The patient is 18–29, male; the lesion involves the head or neck and arm; the photograph is a close-up of the affected area:
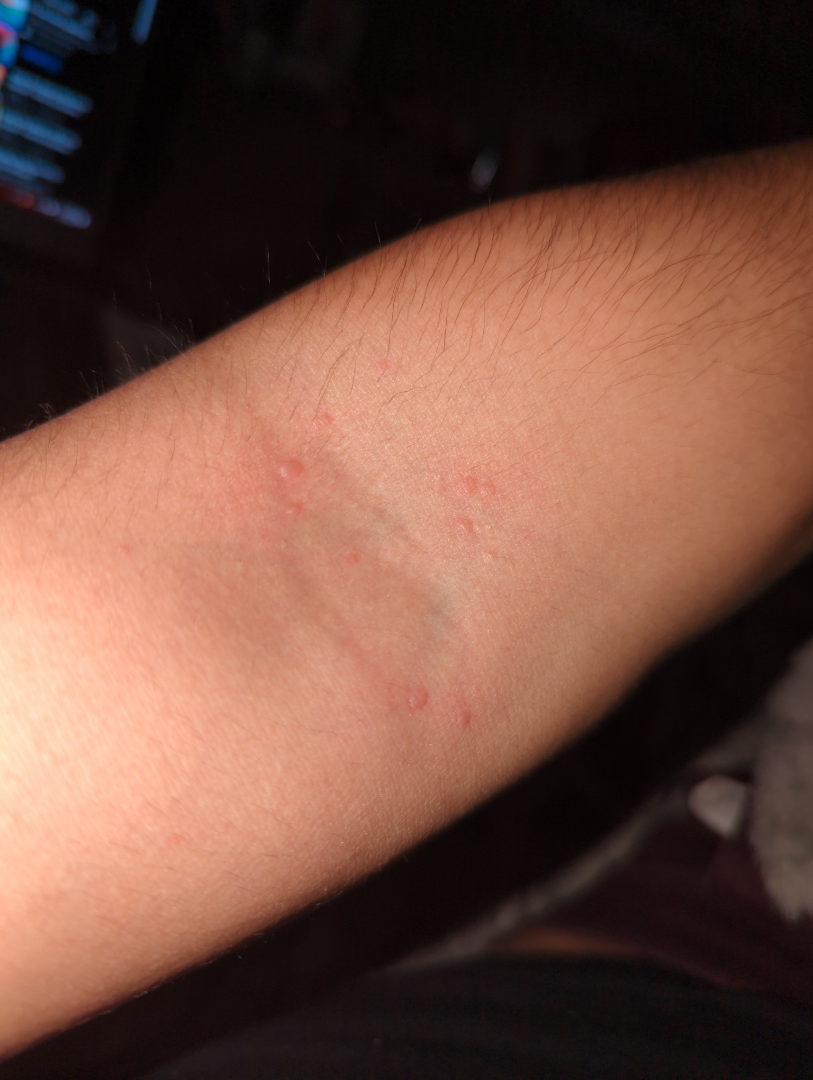differential: the leading impression is Urticaria; an alternative is Eczema; possibly Molluscum Contagiosum.